A dermoscopic image of a skin lesion.
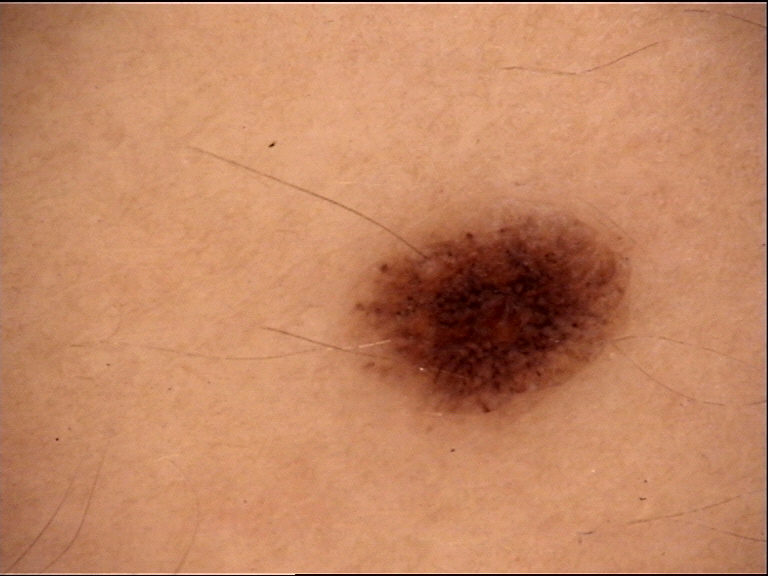– lesion type · banal
– label · junctional nevus (expert consensus)